A subject age 47:
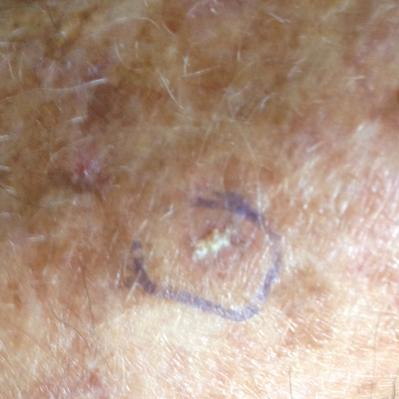Findings: The lesion is located on a forearm. The patient reports that the lesion itches, but does not hurt and has not bled. Conclusion: The clinical impression was an actinic keratosis.